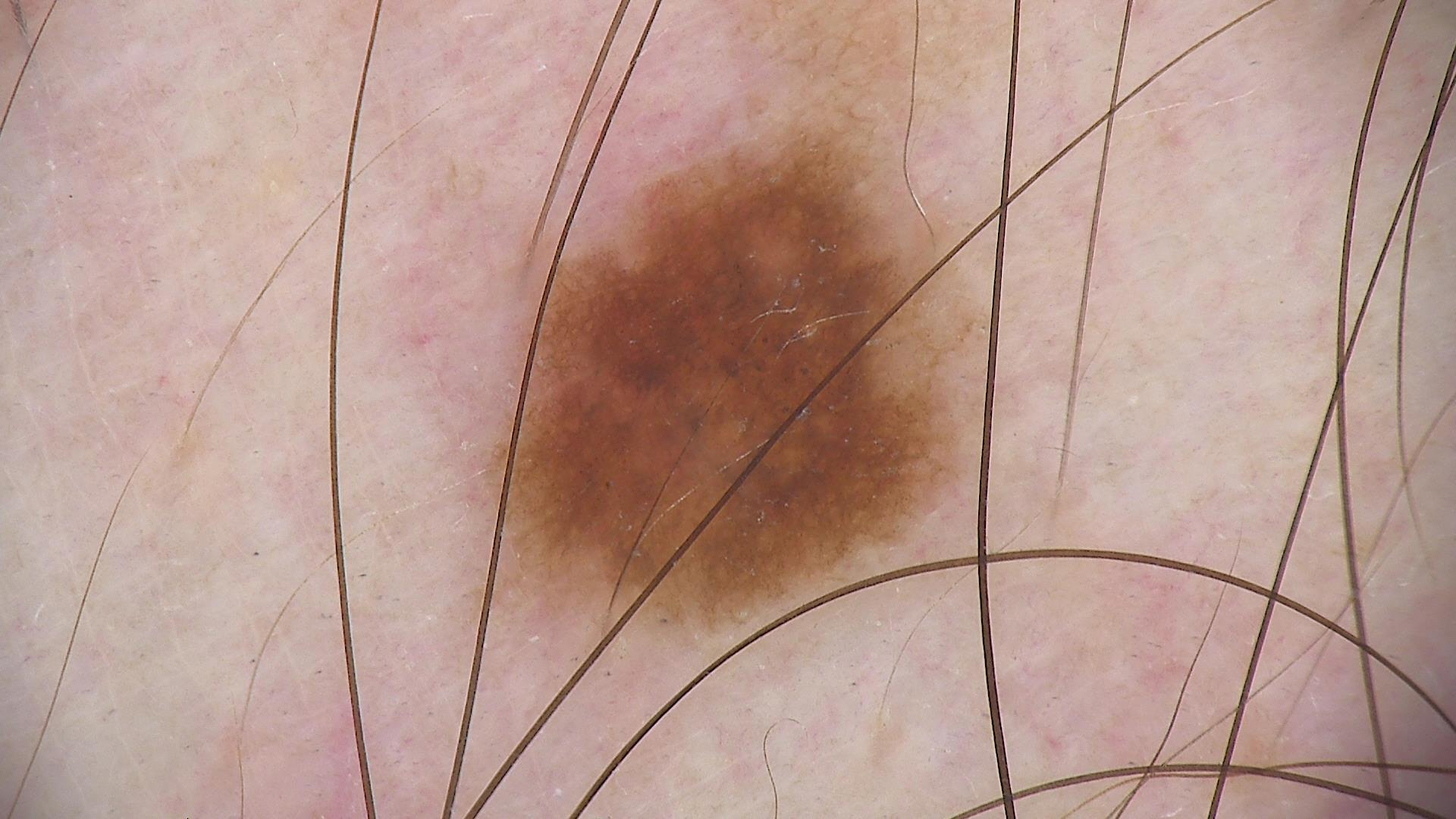A dermoscopic close-up of a skin lesion. Consistent with a benign lesion — a dysplastic junctional nevus.